Texture is reported as raised or bumpy and flat; the patient considered this a rash; present for one to three months; located on the head or neck, back of the hand, arm and palm; this image was taken at a distance; male subject, age 30–39.
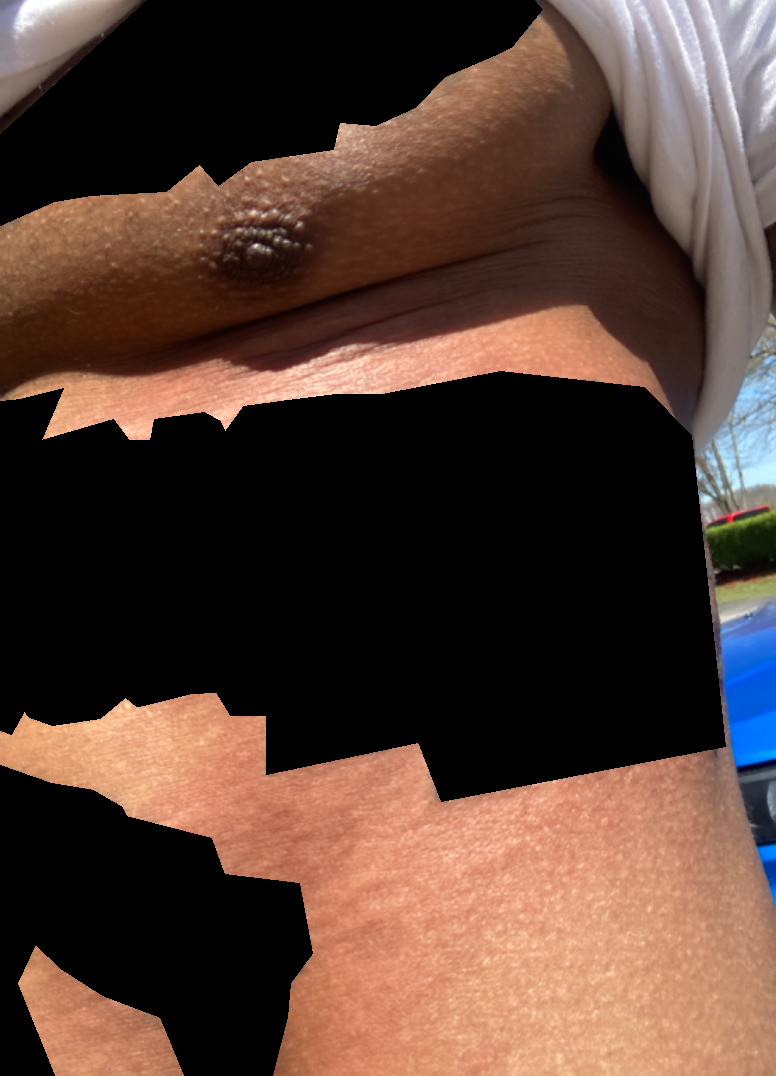No skin condition was discernible on photographic review.